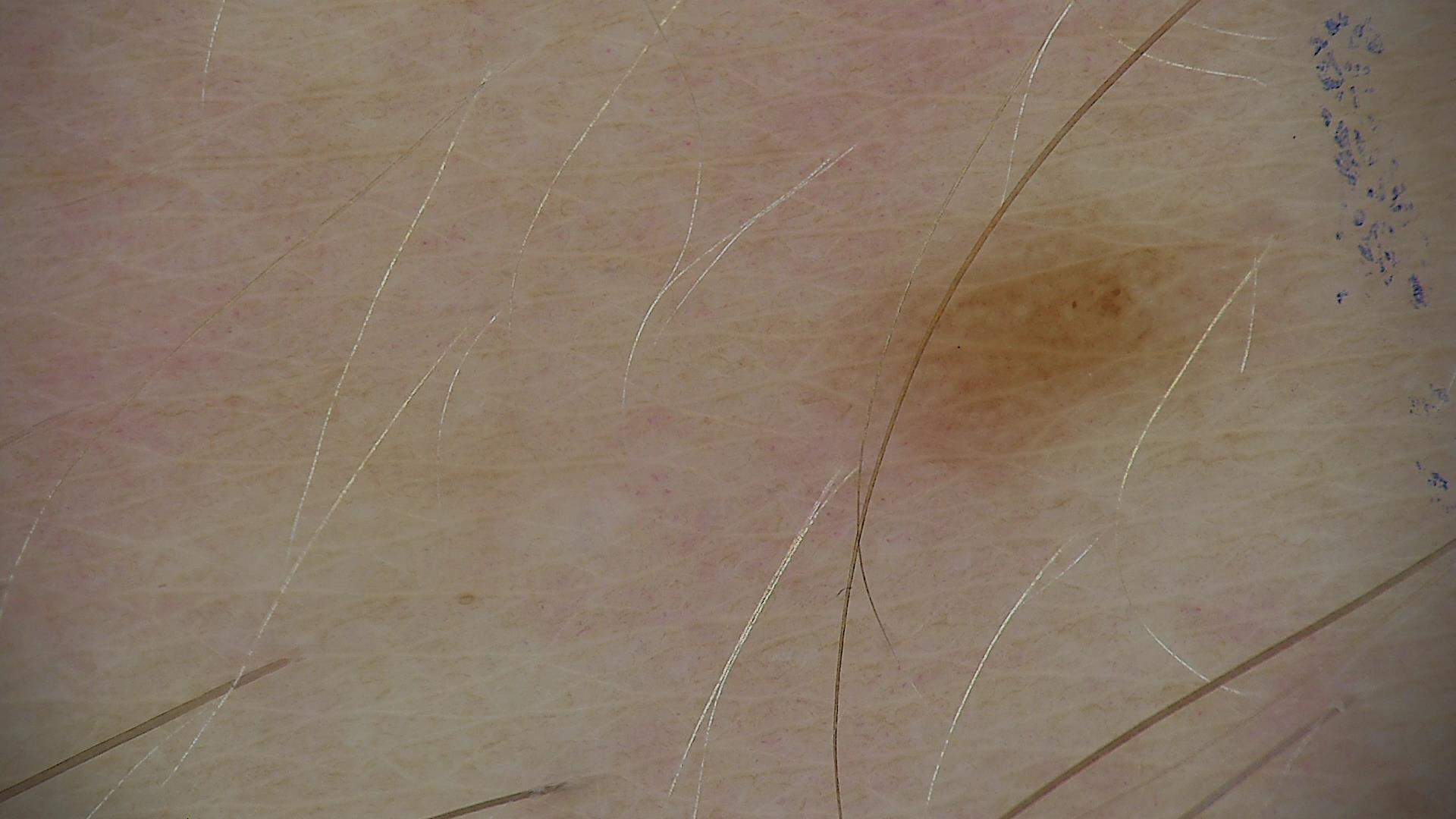A dermoscopic close-up of a skin lesion.
This is a banal lesion.
Diagnosed as a junctional nevus.